The photo was captured at an angle. Female contributor, age 30–39. The patient described the issue as a growth or mole. The contributor reports the lesion is rough or flaky and fluid-filled. The contributor reports the condition has been present for one to four weeks:
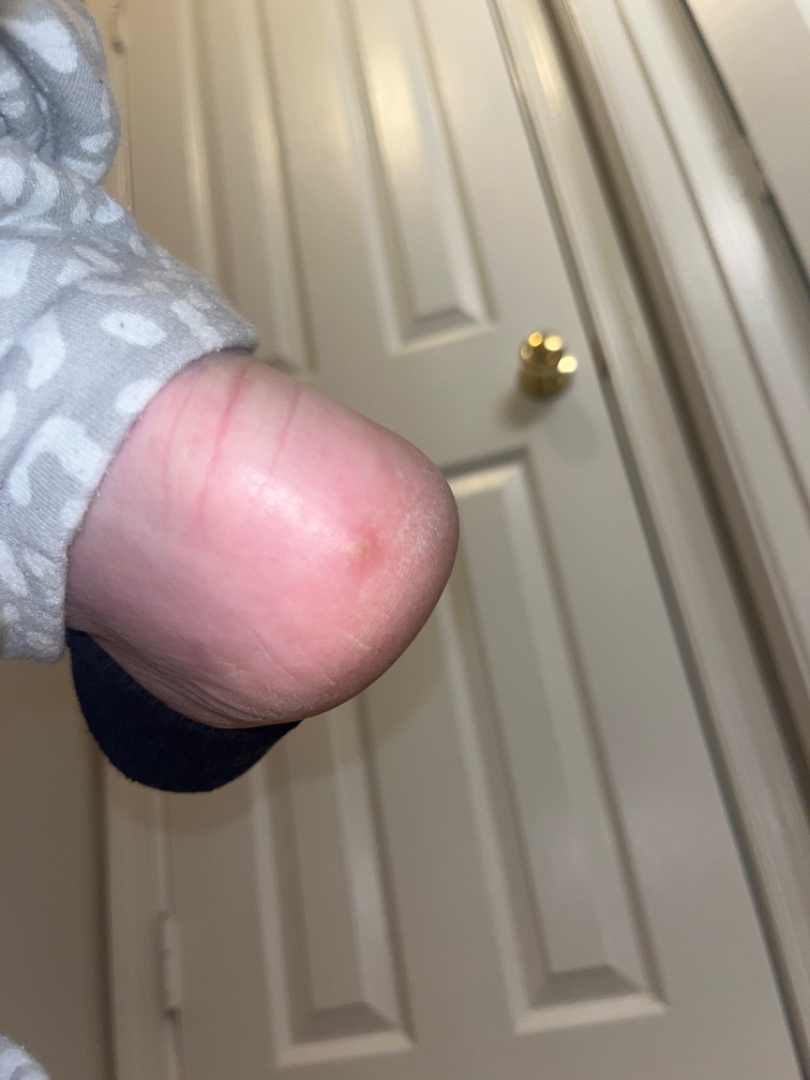assessment = unable to determine.